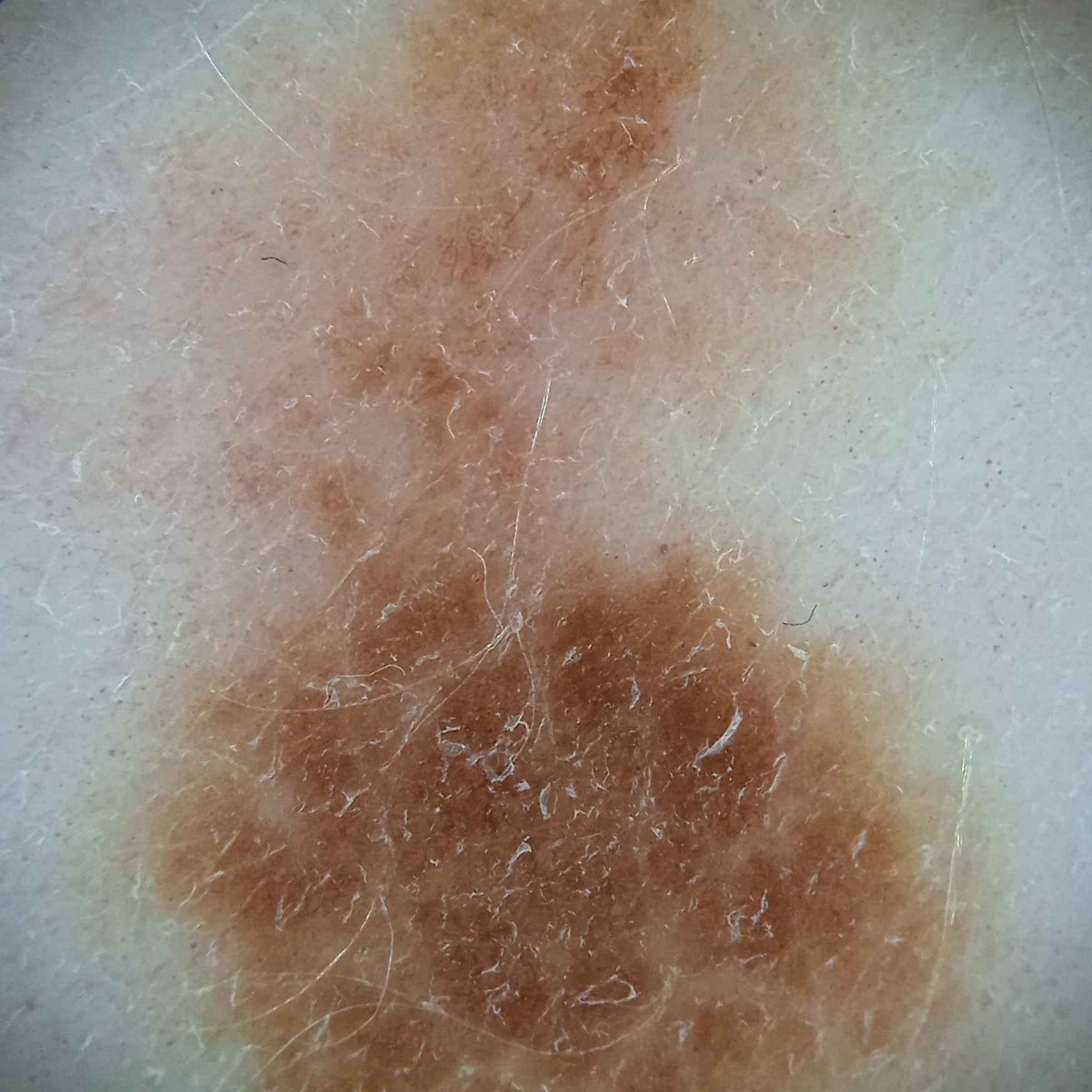Acquired for a research image collection, with no referral diagnosis.
A female patient aged 54.
A dermoscopy image of a skin lesion.
The lesion involves the torso.
Measuring roughly 17.5 mm.
Reviewed by four dermatologists, the consensus diagnosis was a melanoma; the reviewers were not unanimous; diagnostic confidence was moderate.